The head or neck is involved · this is a close-up image — 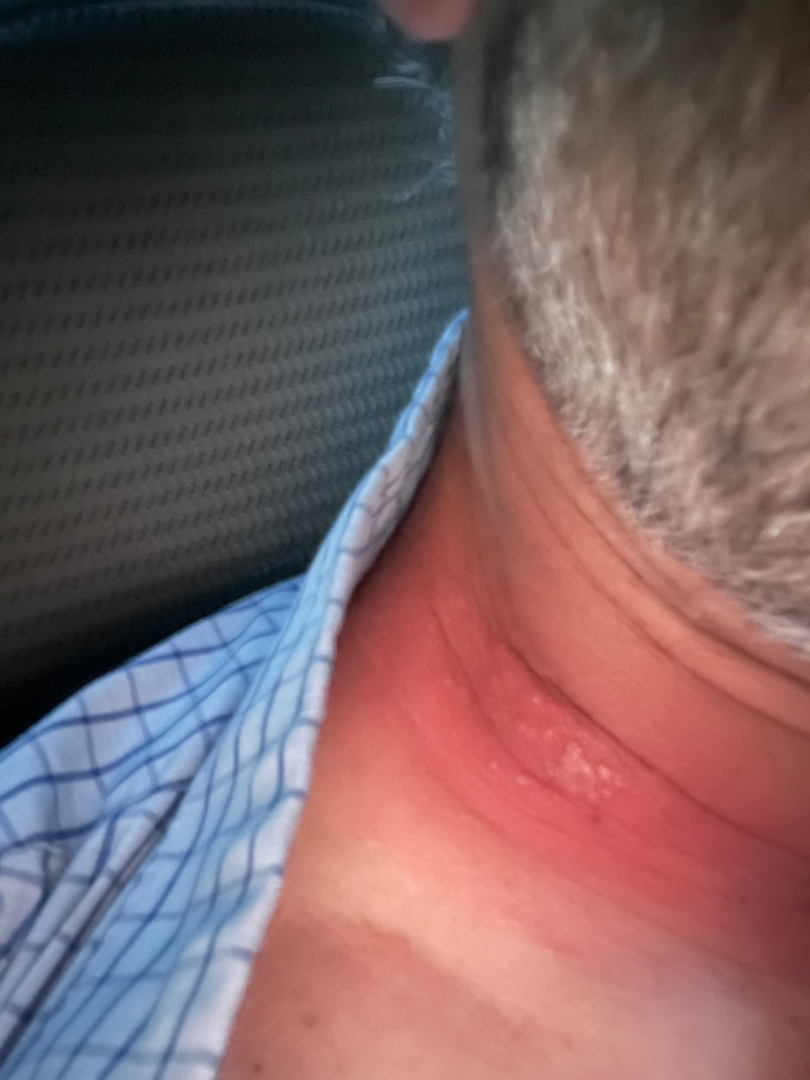Single-reviewer assessment: the leading consideration is Herpes Zoster; also consider Allergic Contact Dermatitis; an alternative is Herpes Simplex.